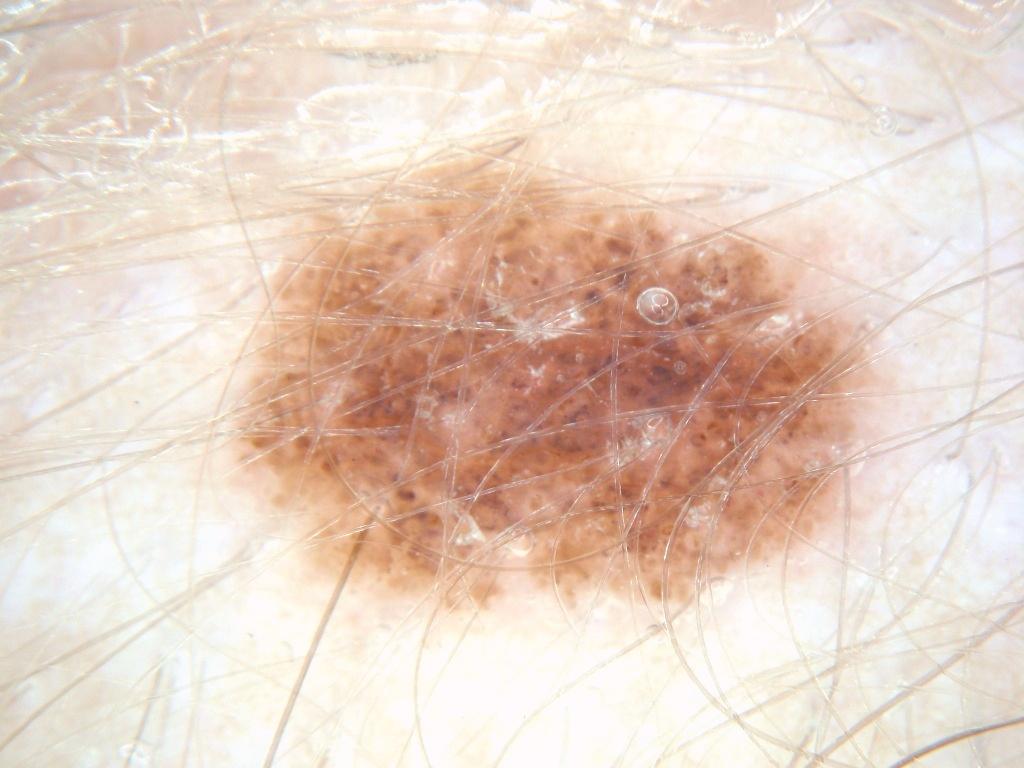A dermoscopic view of a skin lesion.
Lesion location: x1=236, y1=158, x2=877, y2=606.
Consistent with a melanocytic nevus, a benign lesion.